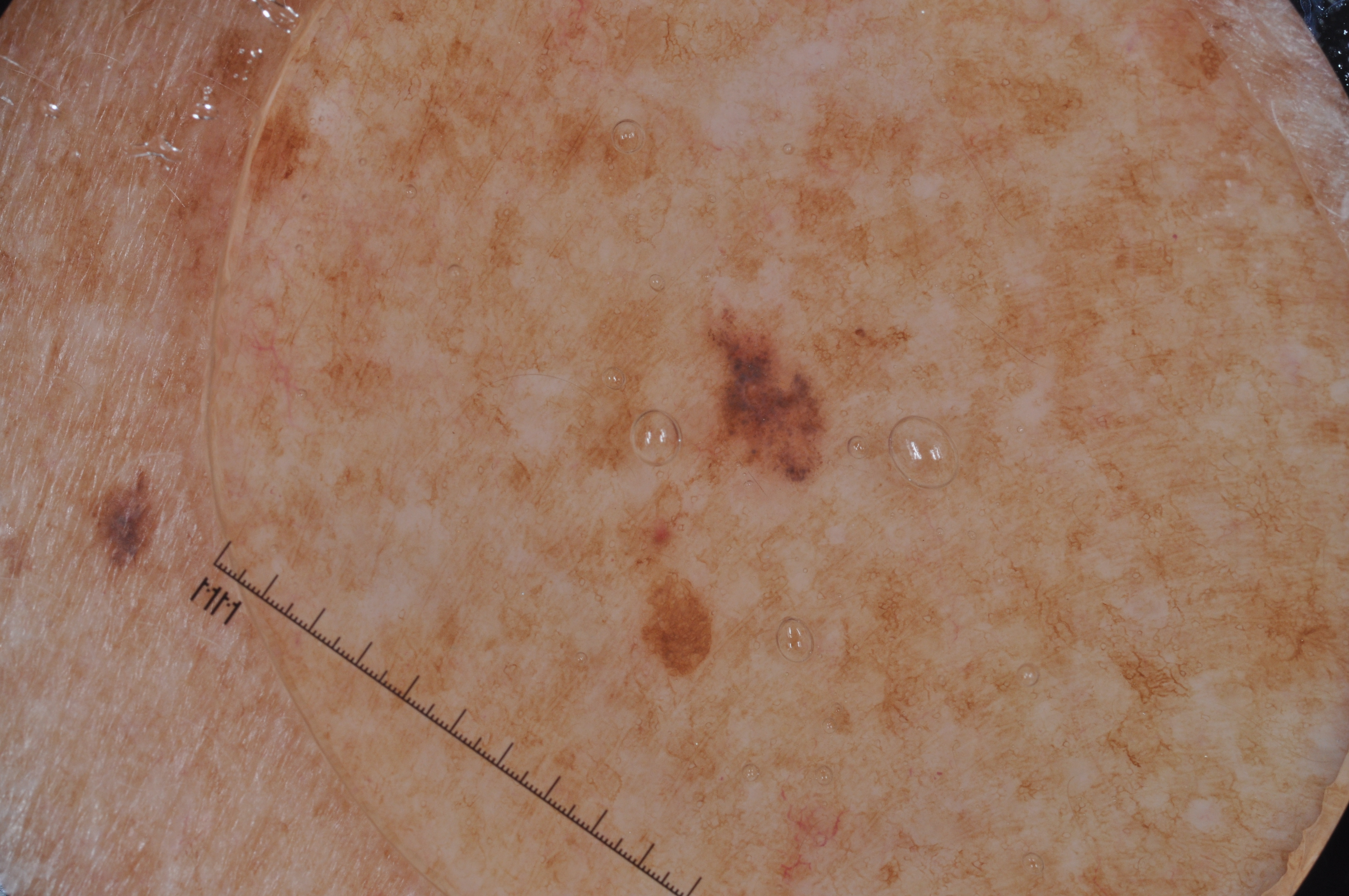| feature | finding |
|---|---|
| subject | female, in their mid- to late 40s |
| image type | dermoscopic image |
| lesion location | (694, 310, 834, 490) |
| absent dermoscopic features | milia-like cysts, streaks, negative network, and pigment network |
| assessment | a melanocytic nevus, a benign lesion |